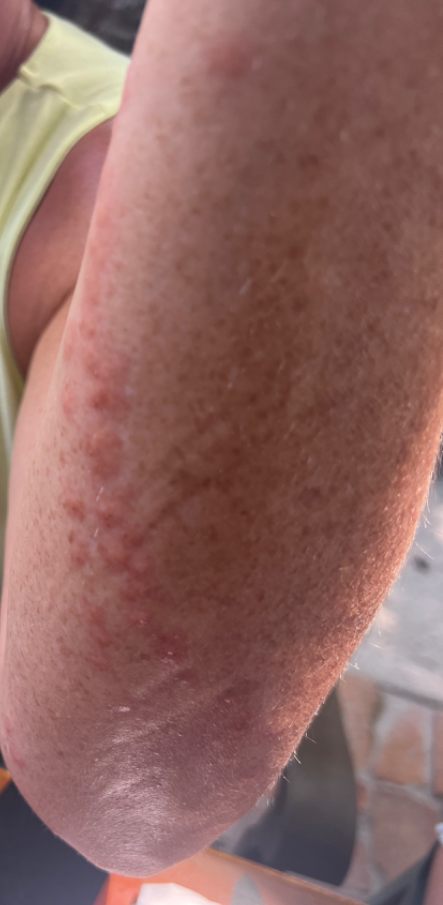Notes:
• assessment · unable to determine
• site · arm and leg
• framing · at an angle